A smartphone photograph of a skin lesion:
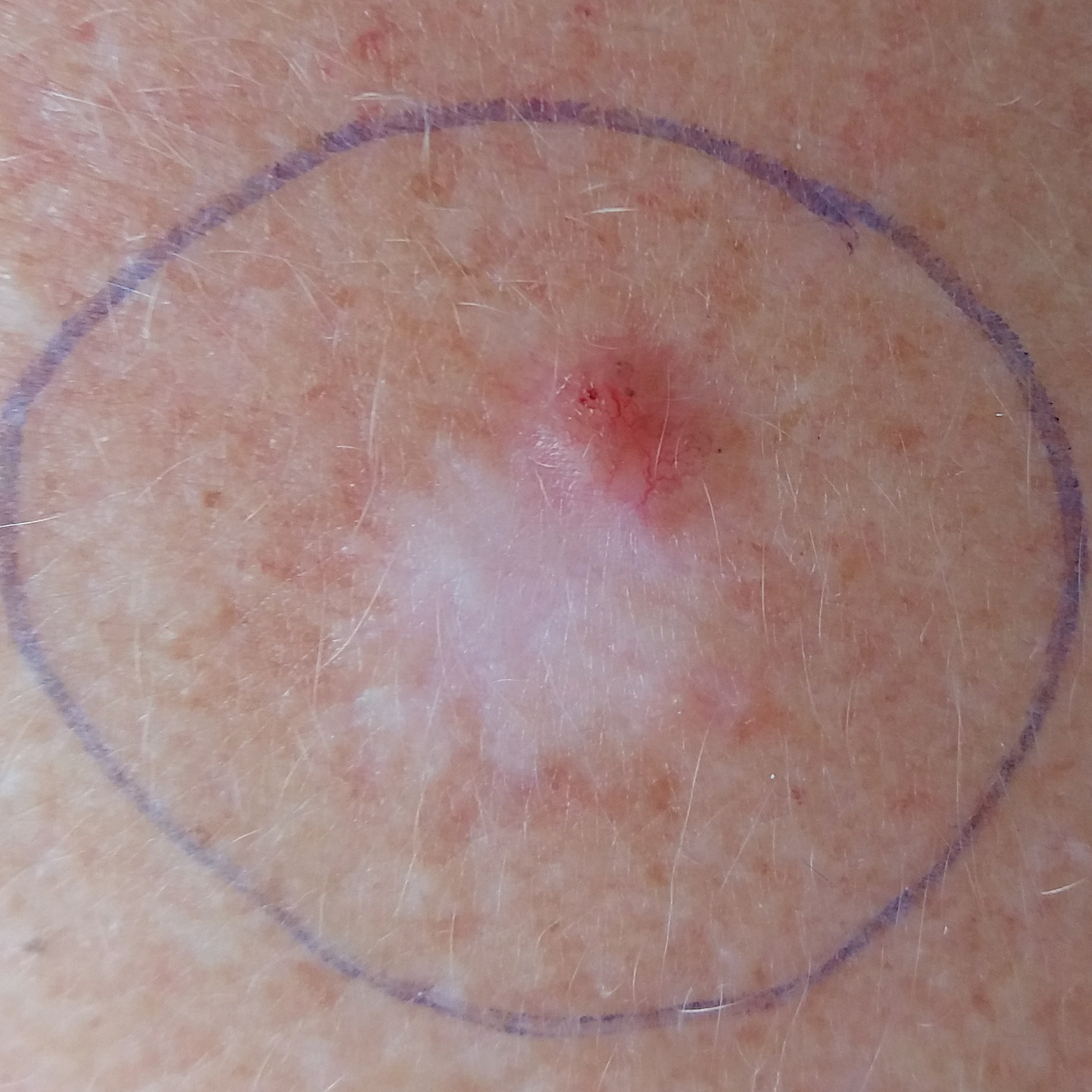Summary:
The lesion involves the neck. By the patient's account, the lesion has changed, is elevated, has grown, has bled, and itches.
Diagnosis:
Histopathologically confirmed as a basal cell carcinoma.